This is a close-up image.
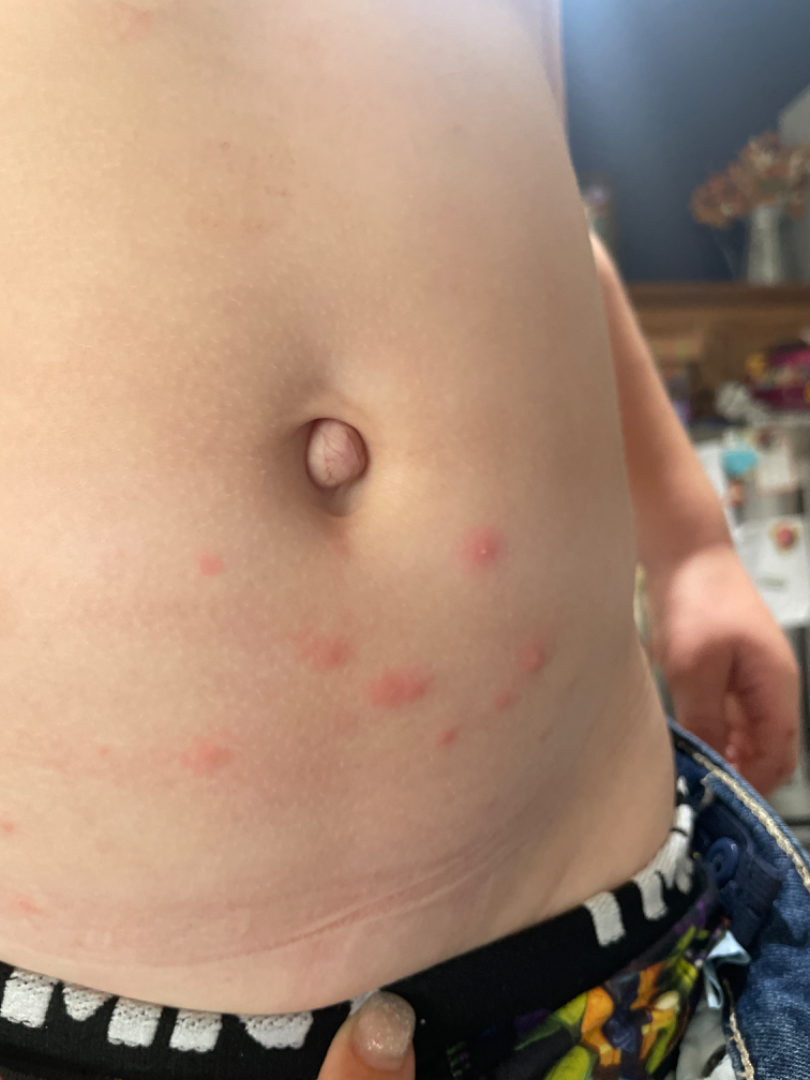Review: On dermatologist assessment of the image: the favored diagnosis is Folliculitis; possibly Insect Bite.